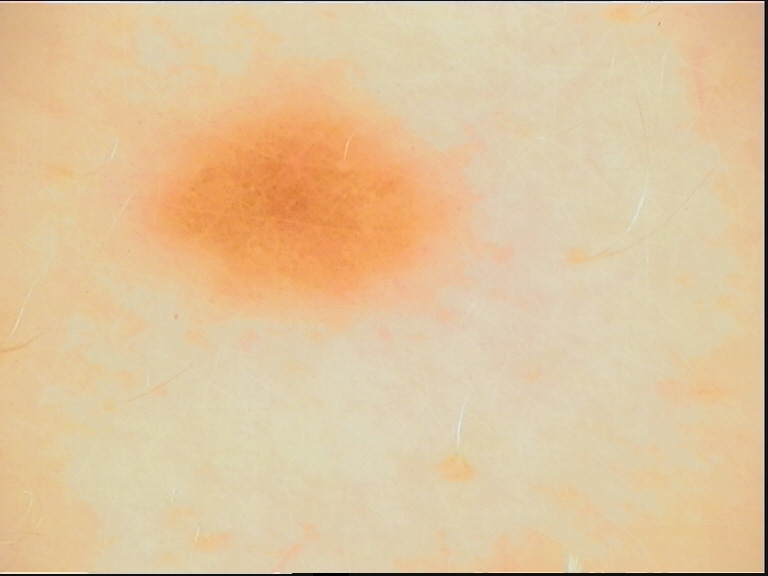The diagnostic label was a banal lesion — a junctional nevus.